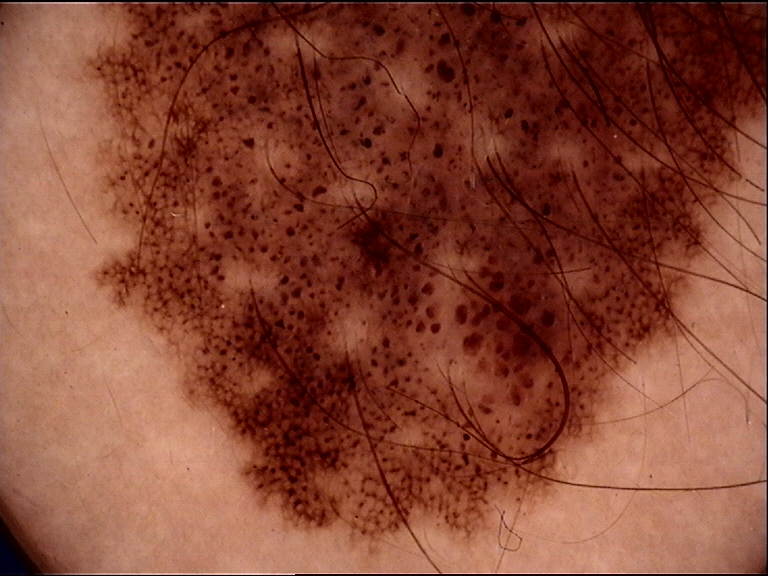Consistent with a congenital compound nevus.